A female patient age 48. A dermoscopic image of a skin lesion. Imaged for a research study, with no referral diagnosis recorded — 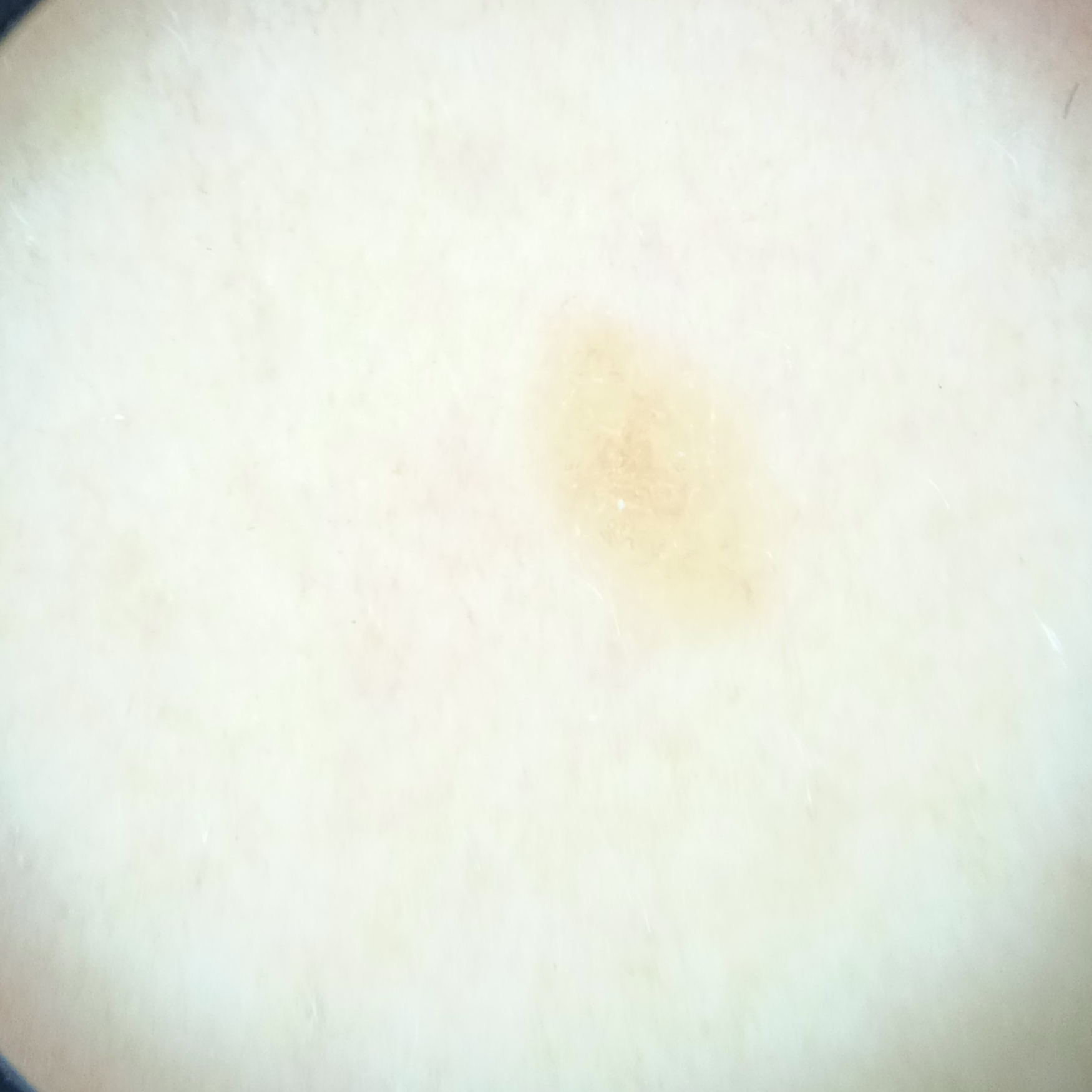The lesion measures approximately 3.8 mm. The consensus diagnosis for this lesion was a seborrheic keratosis.